A female patient age 15 · imaged for a research study, with no referral diagnosis recorded:
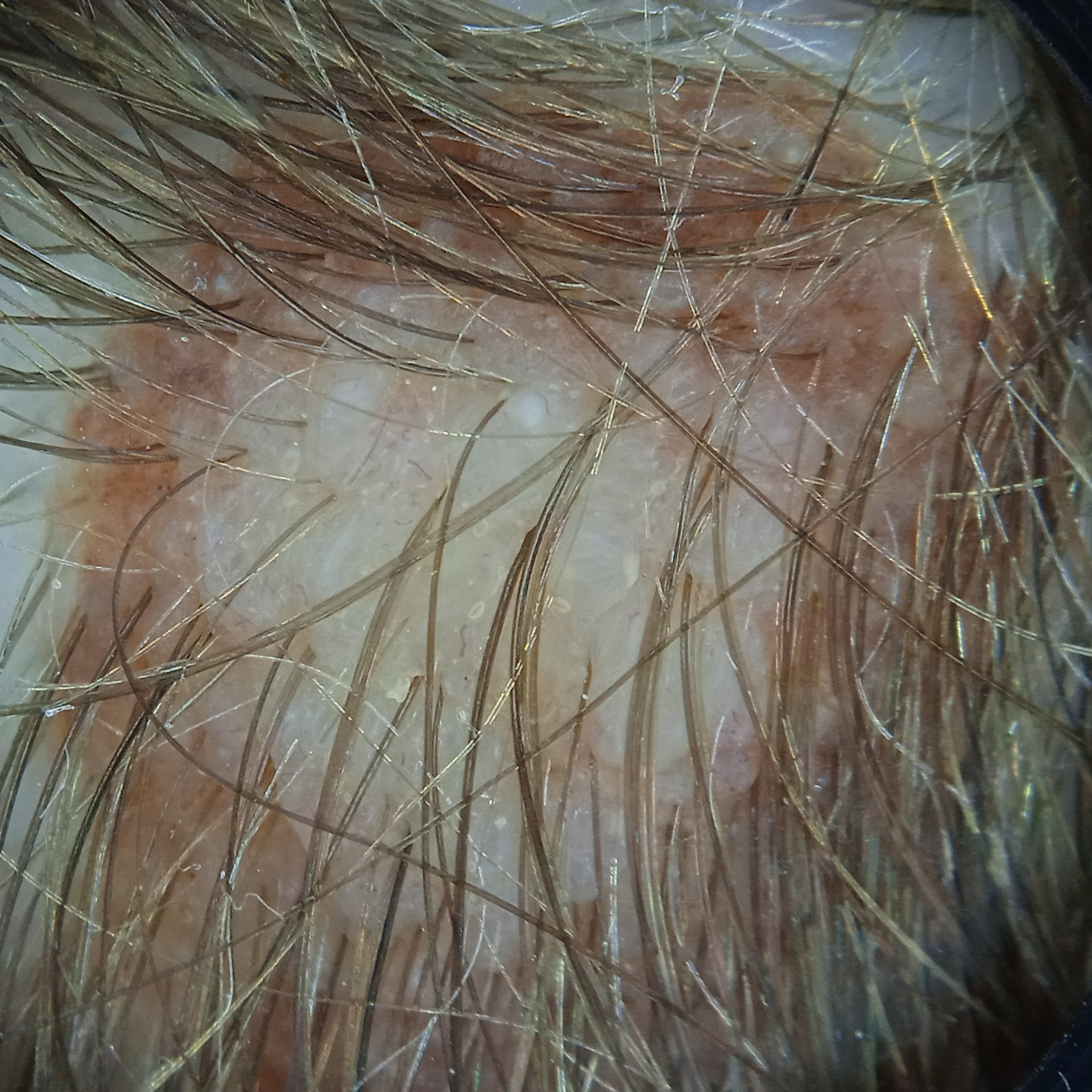Q: What is the anatomic site?
A: the head
Q: Lesion size?
A: 9.1 mm
Q: What was the diagnosis?
A: melanocytic nevus (dermatologist consensus)